The photograph was taken at an angle — 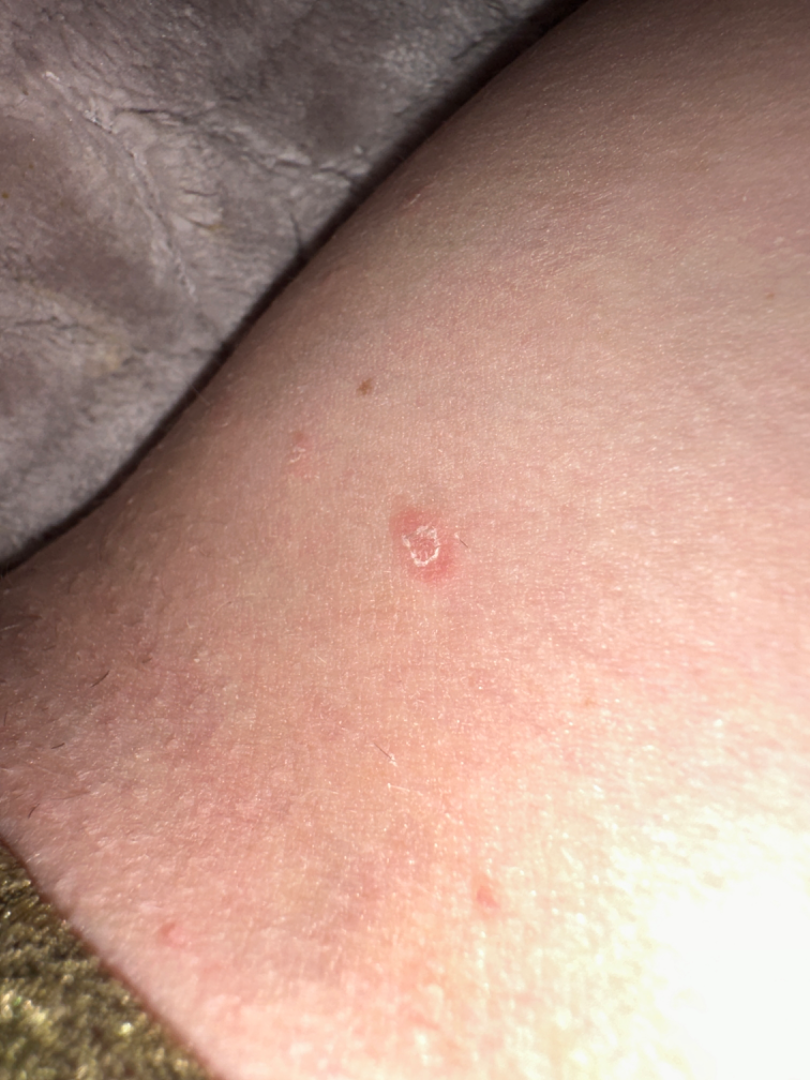Skin tone: Fitzpatrick phototype II; human graders estimated Monk skin tone scale 6 (US pool) or 2 (India pool). The patient considered this a rash. Present for one to four weeks. Associated systemic symptoms include chills and fatigue. Texture is reported as flat and rough or flaky. The favored diagnosis is Pityriasis rosea; also raised was Psoriasis.